The lesion involves the leg, the photograph was taken at an angle — 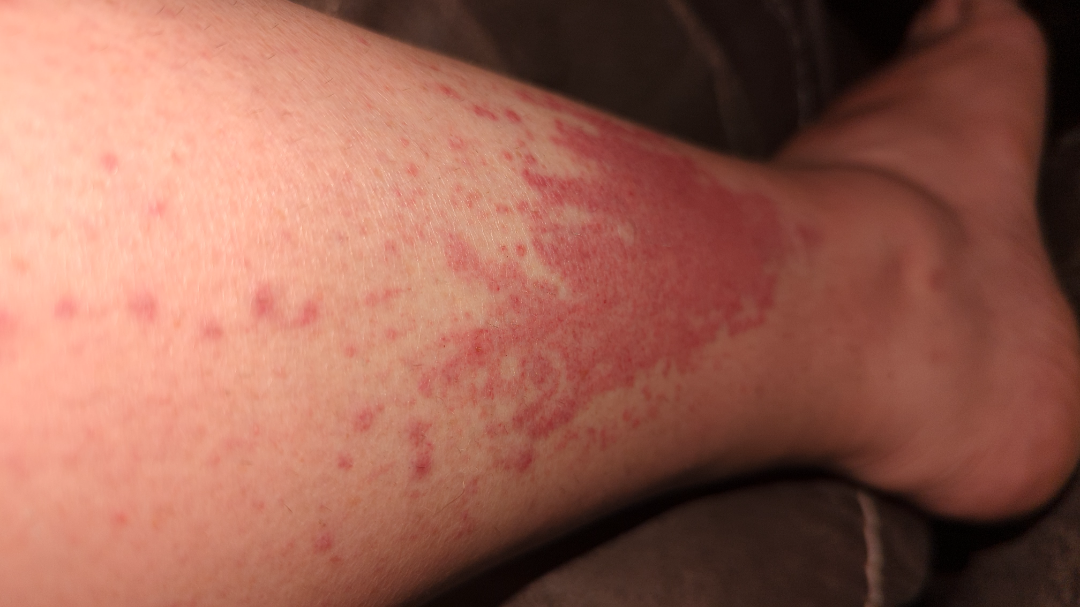  symptoms:
    - itching
    - bothersome appearance
    - burning
  patient_category: a rash
  duration: less than one week
  skin_tone:
    fitzpatrick: II
    monk_skin_tone: 2
  texture: raised or bumpy
  differential:
    tied_lead:
      - Allergic Contact Dermatitis
      - Leukocytoclastic Vasculitis
    unlikely:
      - Abrasion, scrape, or scab